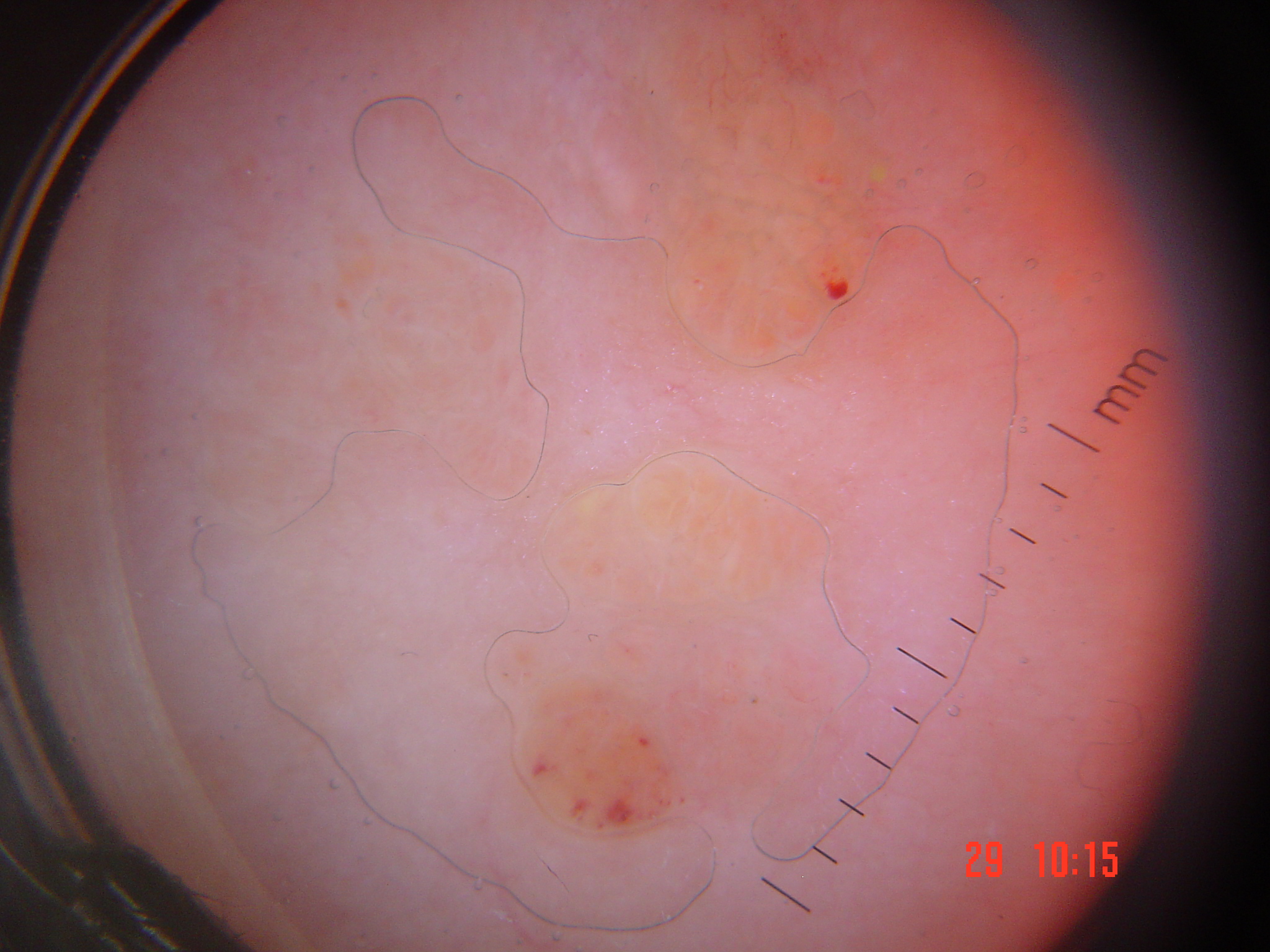subtype = vascular; diagnosis = lymphangioma (expert consensus).